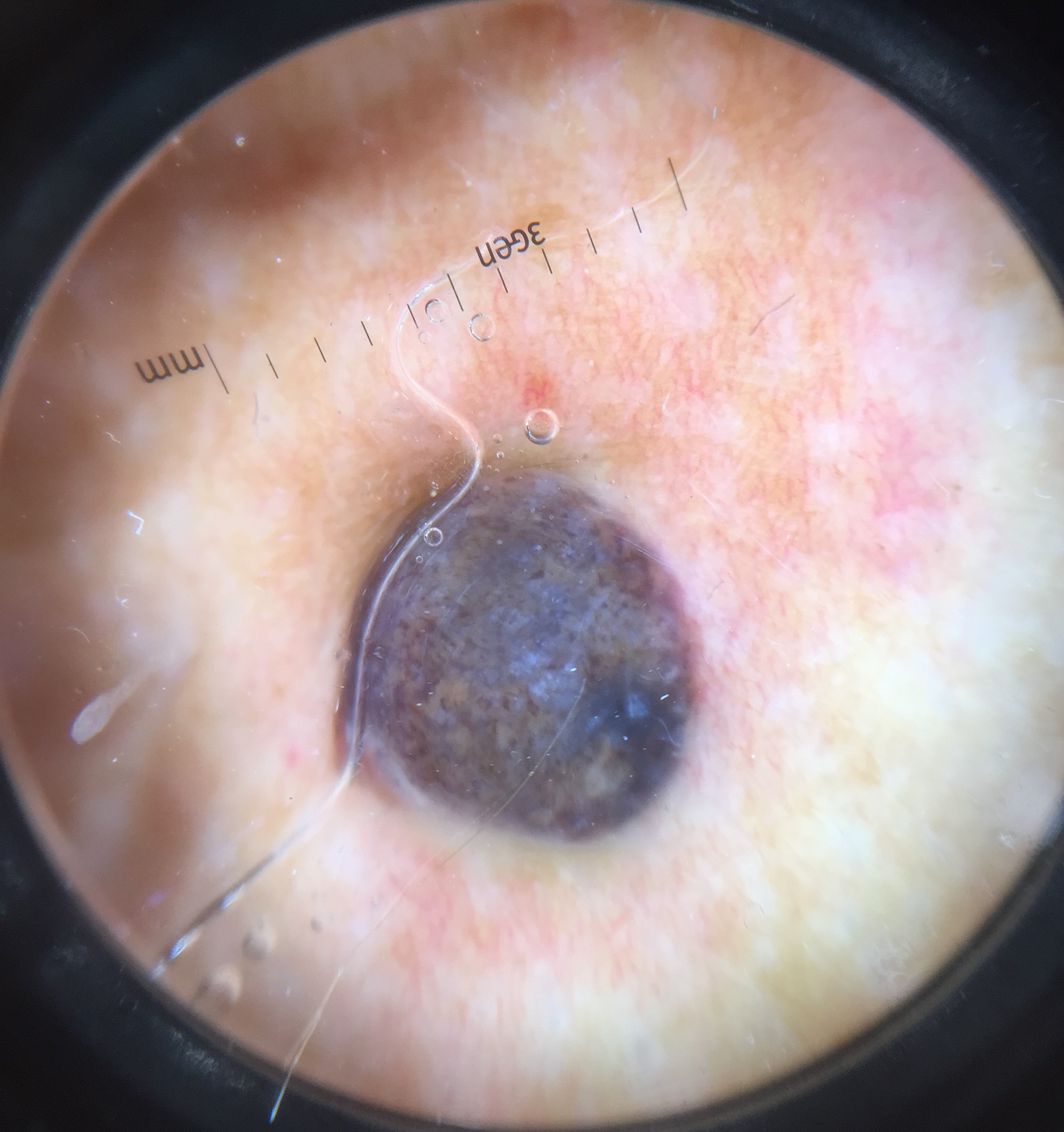* diagnostic label: melanoma (biopsy-proven)